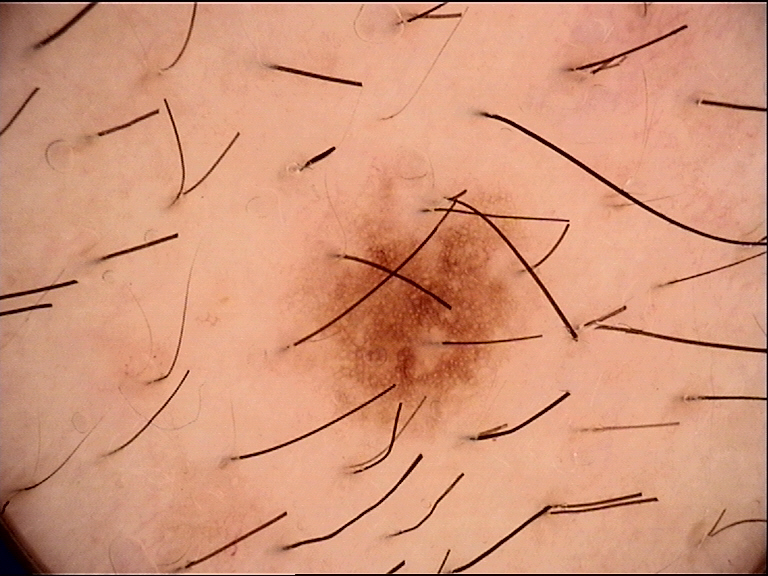label: dysplastic junctional nevus (expert consensus).